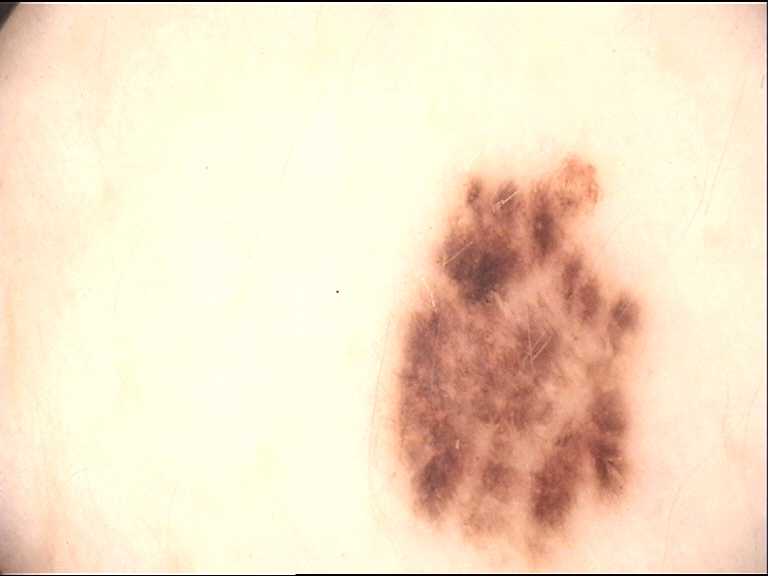modality — dermoscopy
label — dysplastic junctional nevus (expert consensus)